A dermoscopic photograph of a skin lesion:
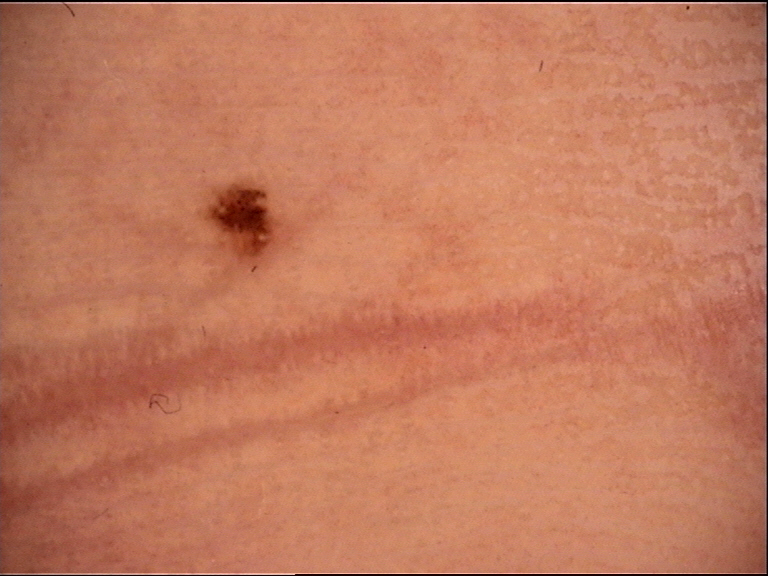The architecture is that of a banal lesion. Classified as an acral junctional nevus.